The patient is 18–29, female. The affected area is the back of the torso and front of the torso. The photo was captured at a distance — 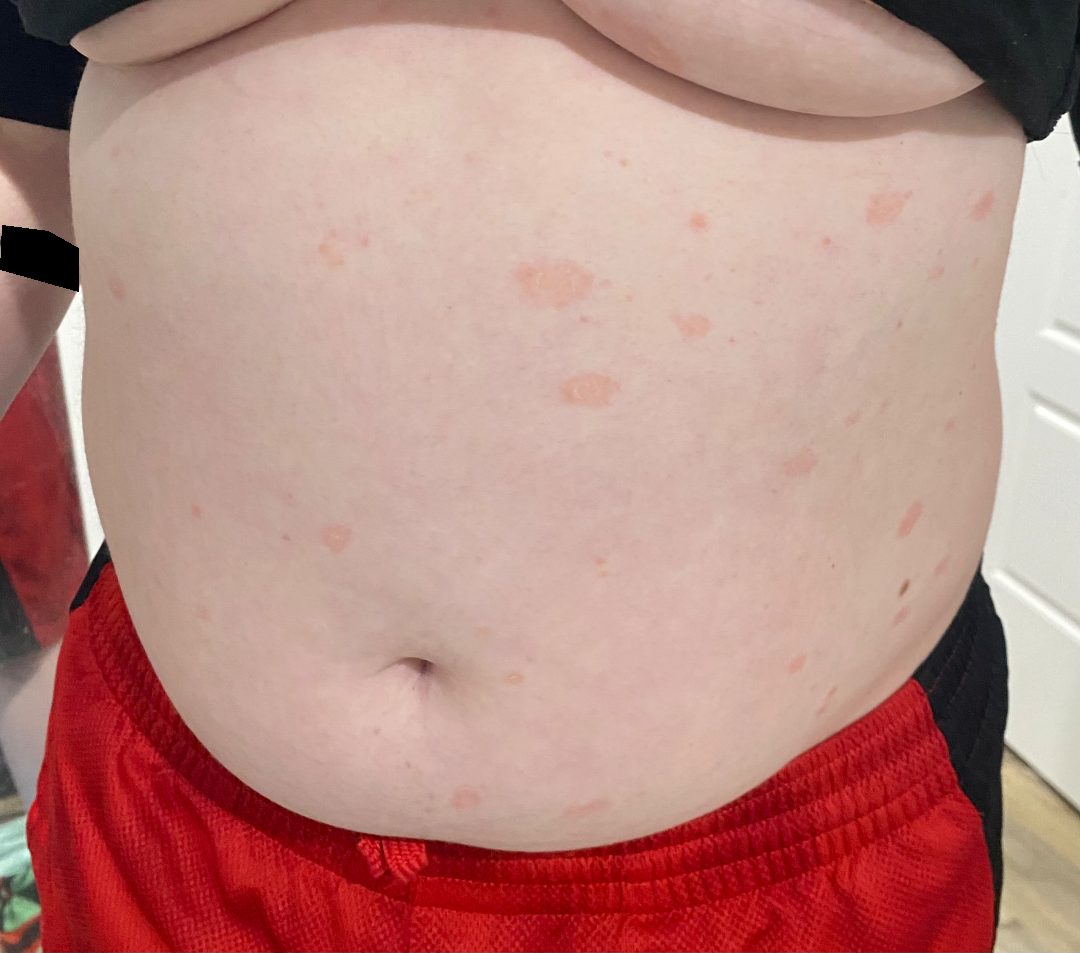Findings:
• patient-reported symptoms · enlargement and bothersome appearance
• described texture · rough or flaky and raised or bumpy
• history · one to four weeks
• clinical impression · most consistent with Pityriasis rosea; also on the differential is Psoriasis; less probable is Eczema